The lesion involves the top or side of the foot and leg · Fitzpatrick skin type III; human graders estimated Monk Skin Tone 1 or 2 · symptoms reported: bothersome appearance and itching · an image taken at an angle · texture is reported as raised or bumpy · present for one to three months:
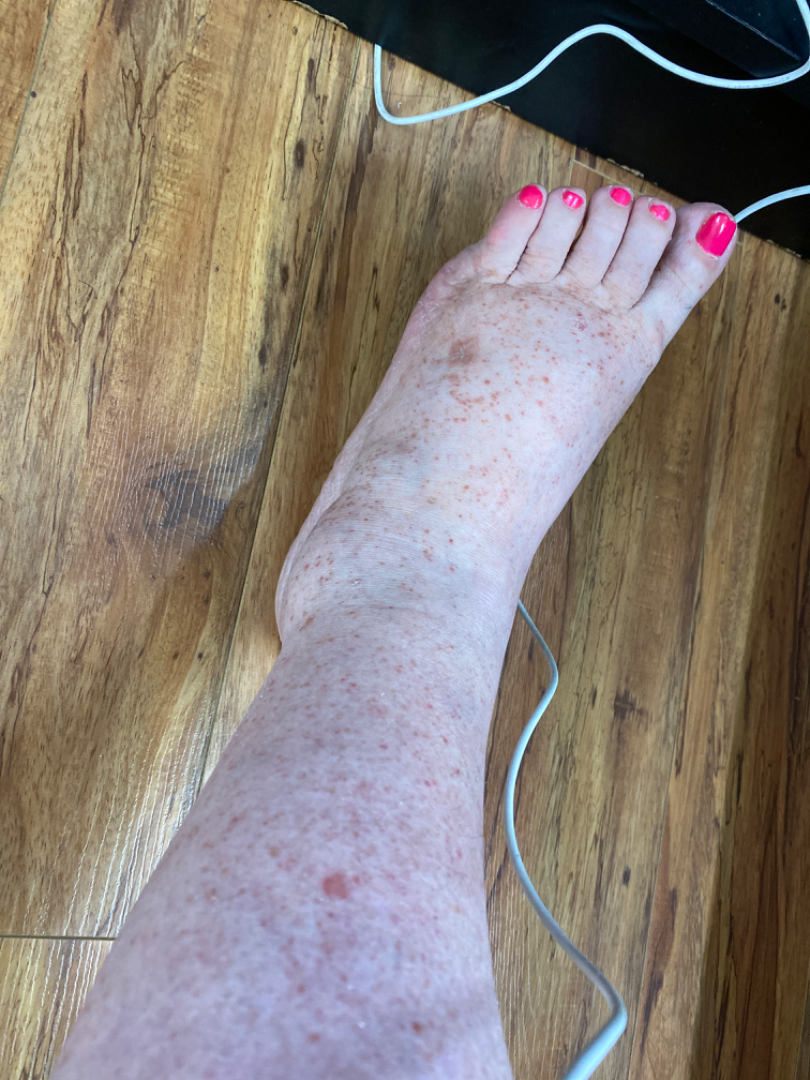Impression:
On teledermatology review: Pigmented purpuric eruption (possible); Leukocytoclastic Vasculitis (possible).